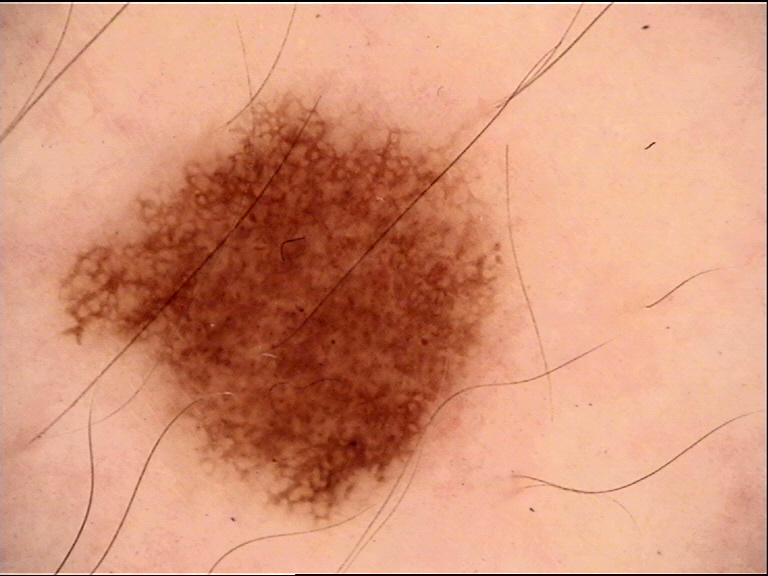Findings:
• imaging: dermoscopy
• class: dysplastic junctional nevus (expert consensus)